The lesion involves the back of the hand, front of the torso, arm and head or neck. An image taken at an angle. The patient is 18–29, female: 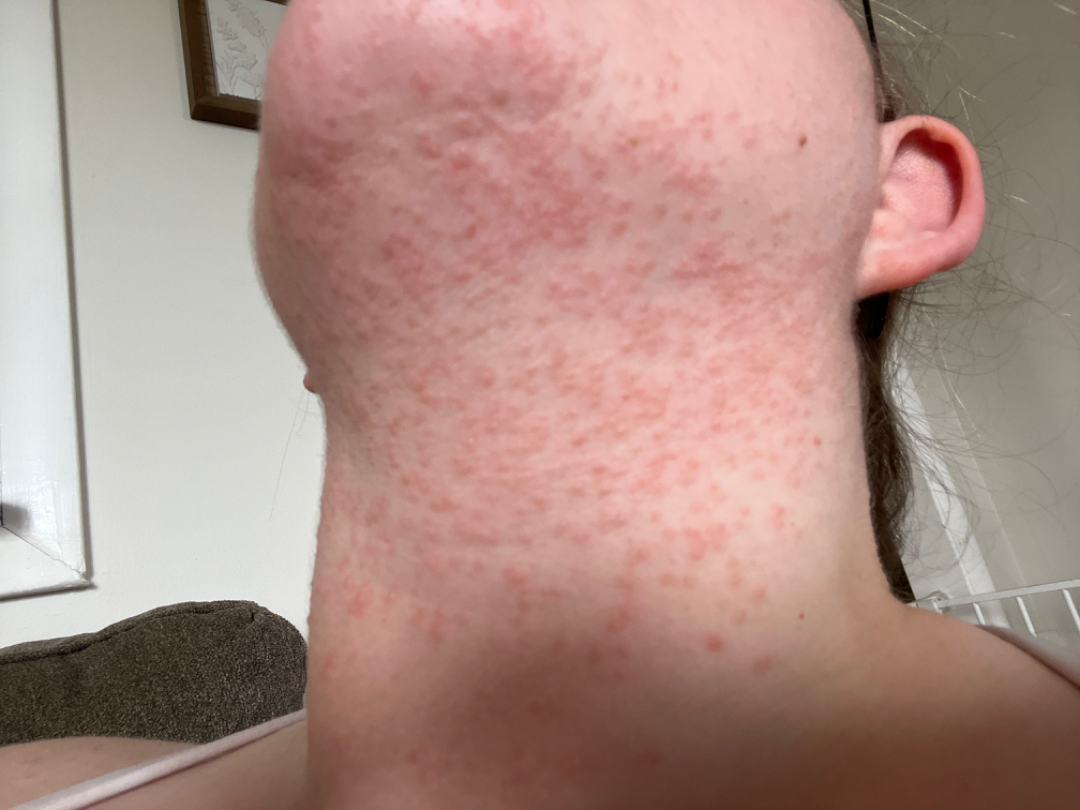Favoring Acne; also on the differential is Folliculitis.